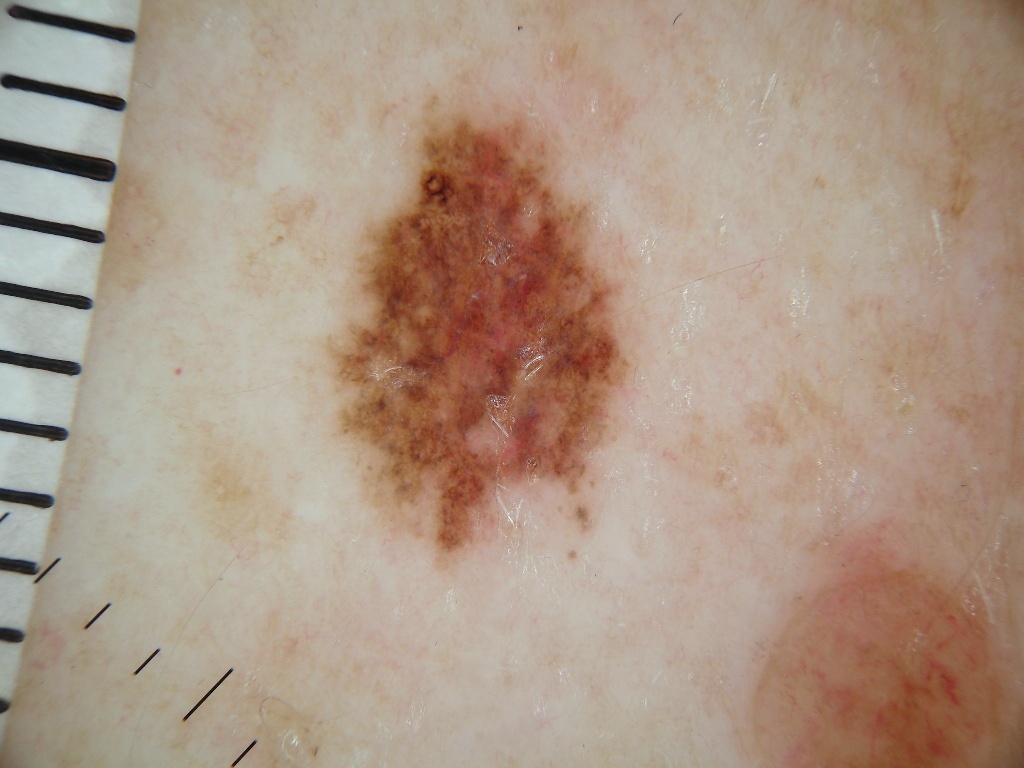The subject is a male in their 70s.
A skin lesion imaged with a dermatoscope.
In (x1, y1, x2, y2) order, the visible lesion spans (323, 63, 634, 567).
Dermoscopic assessment notes globules; no pigment network, negative network, milia-like cysts, or streaks.
The lesion covers approximately 13% of the dermoscopic field.
The lesion was assessed as a melanocytic nevus.